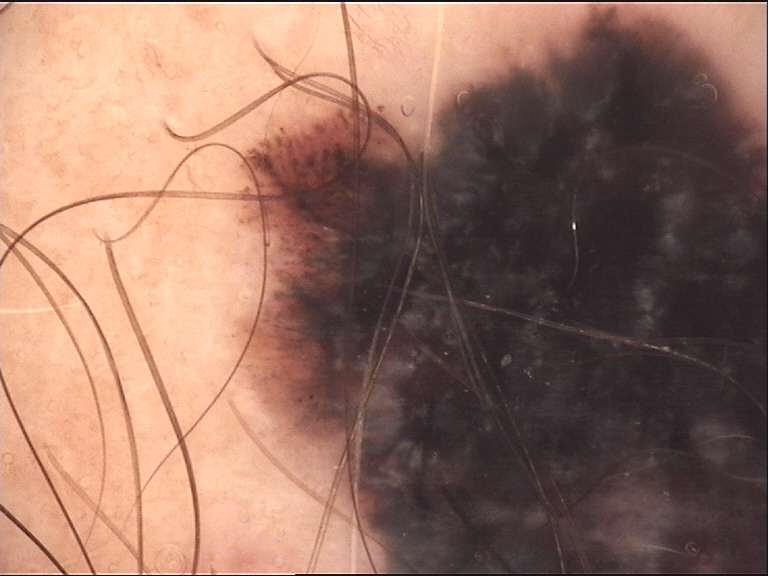Summary:
A dermatoscopic image of a skin lesion.
Pathology:
The biopsy diagnosis was a melanoma.